A male patient roughly 60 years of age.
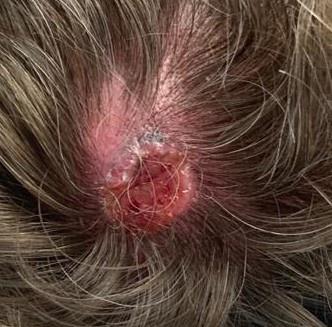The lesion involves the head or neck. Histopathologically confirmed as a melanoma.